The photograph is a close-up of the affected area:
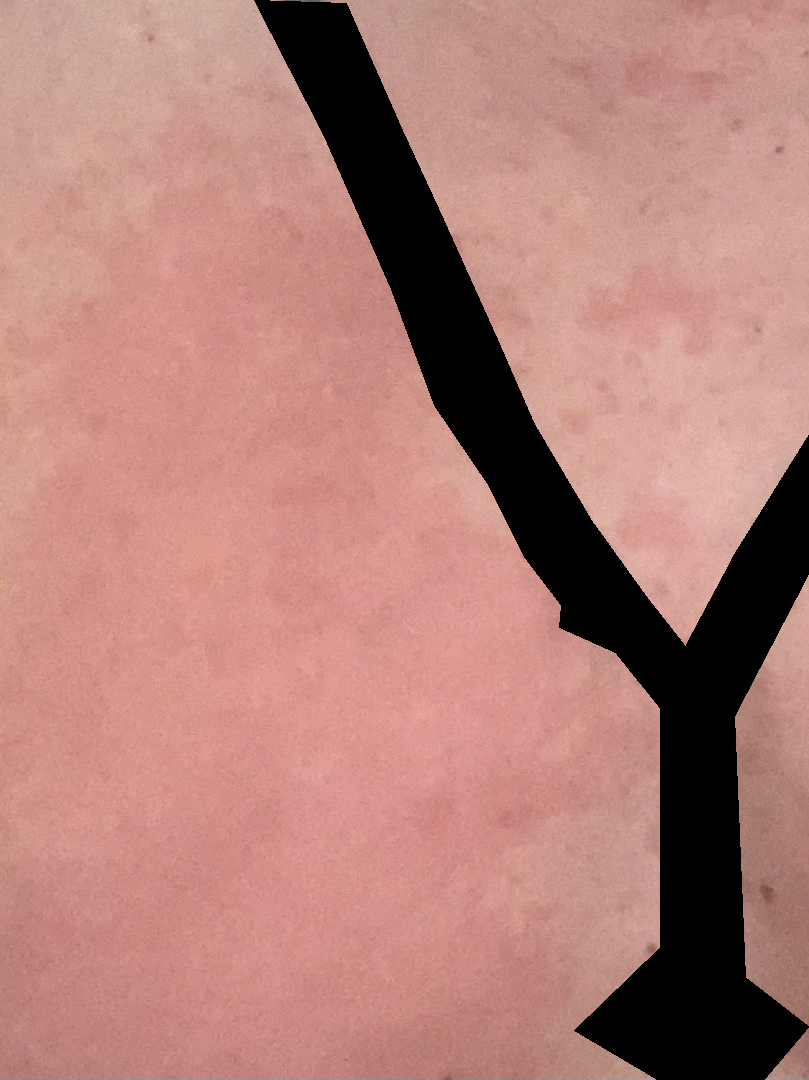Findings: The case was indeterminate on photographic review.